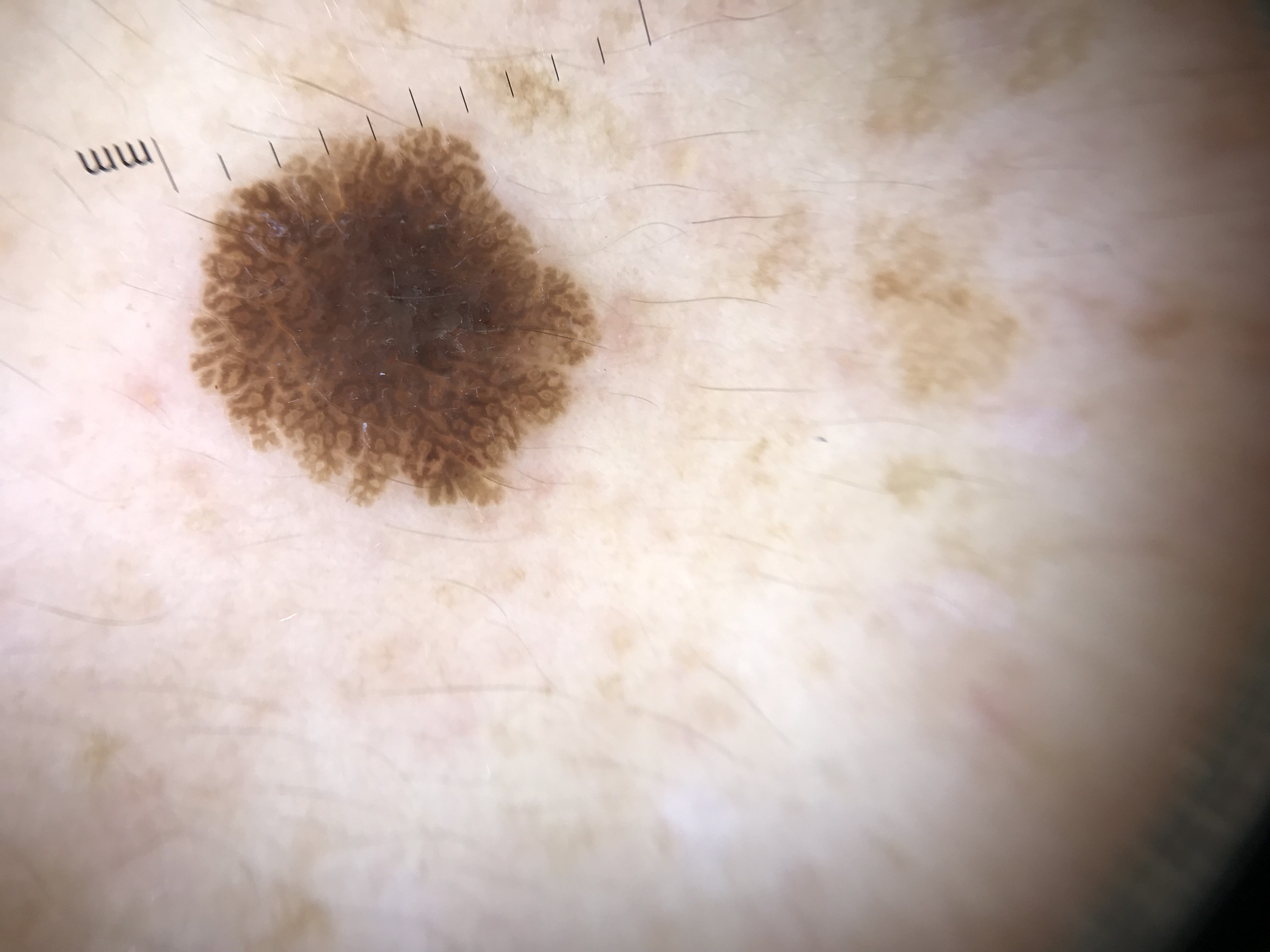Dermoscopy of a skin lesion.
Classified as a seborrheic keratosis.